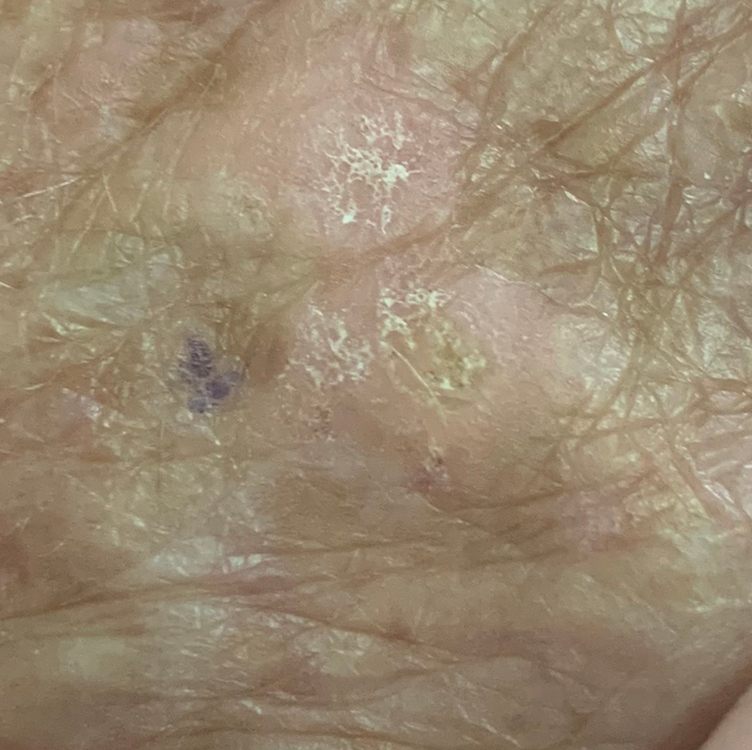A smartphone photograph of a skin lesion.
Fitzpatrick phototype II.
A female patient in their 70s.
The lesion is on a hand.
The lesion measures 8 × 7 mm.
Per patient report, the lesion itches, but does not hurt.
On biopsy, the diagnosis was an actinic keratosis.